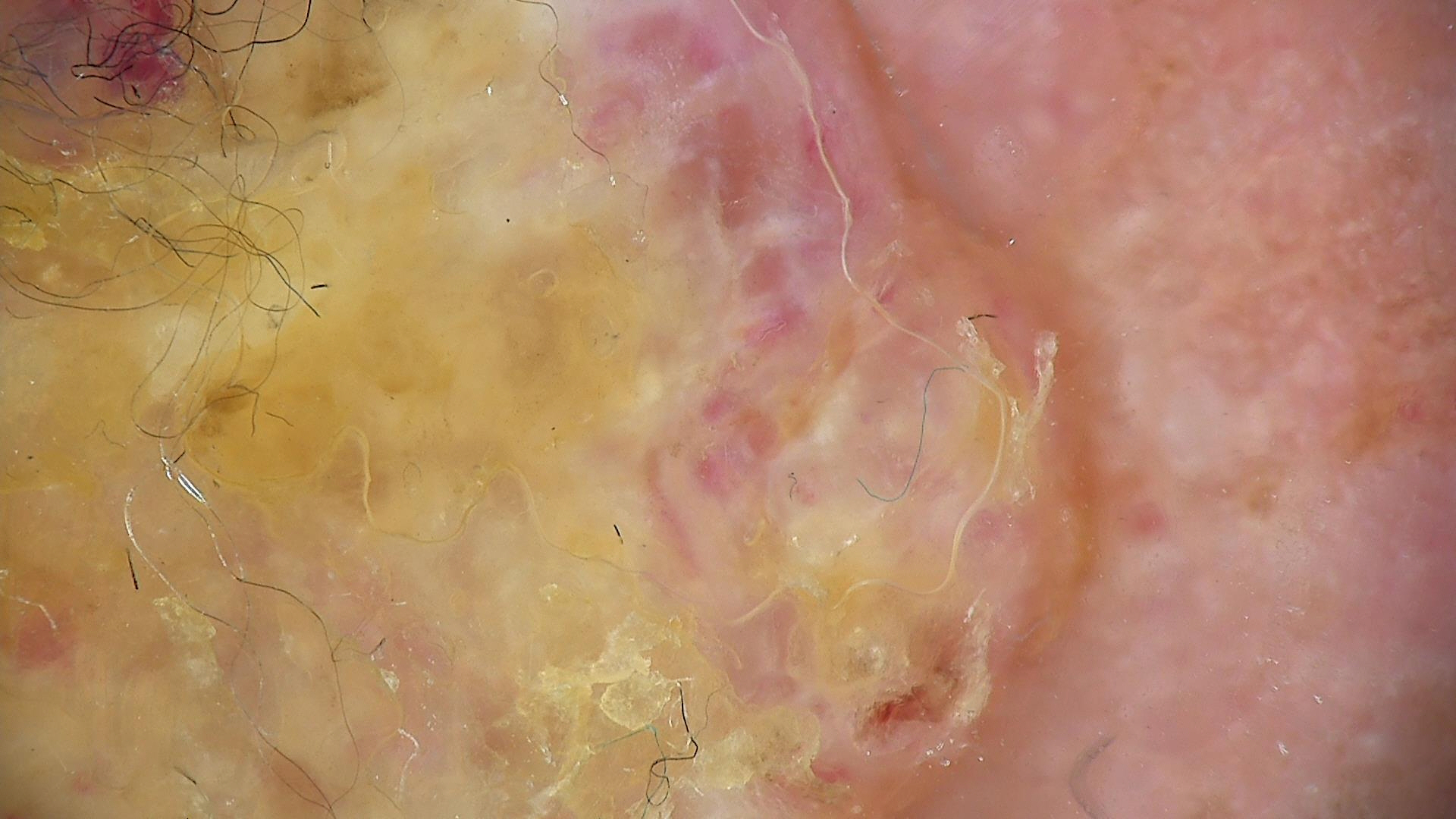image = dermatoscopy, class = squamous cell carcinoma (biopsy-proven).